The leg is involved; no associated systemic symptoms reported; the lesion is described as fluid-filled and raised or bumpy; the patient considered this a rash; the photograph was taken at a distance; the patient indicates the condition has been present for three to twelve months; the lesion is associated with bothersome appearance, burning, itching and enlargement — 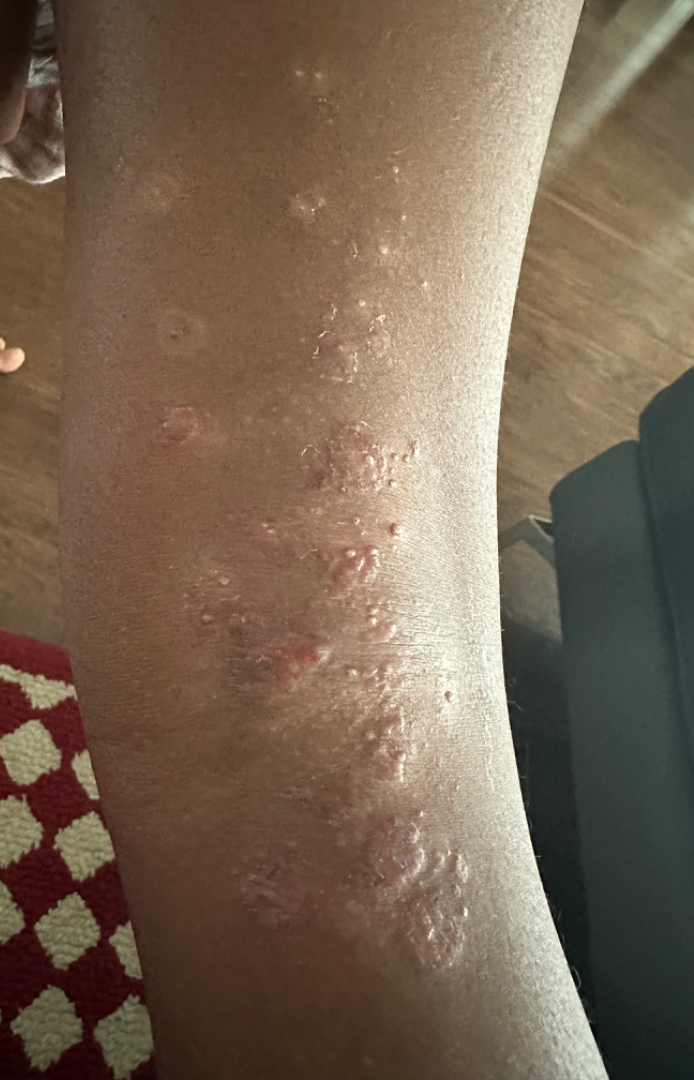assessment — not assessable.